A skin lesion imaged with a dermatoscope.
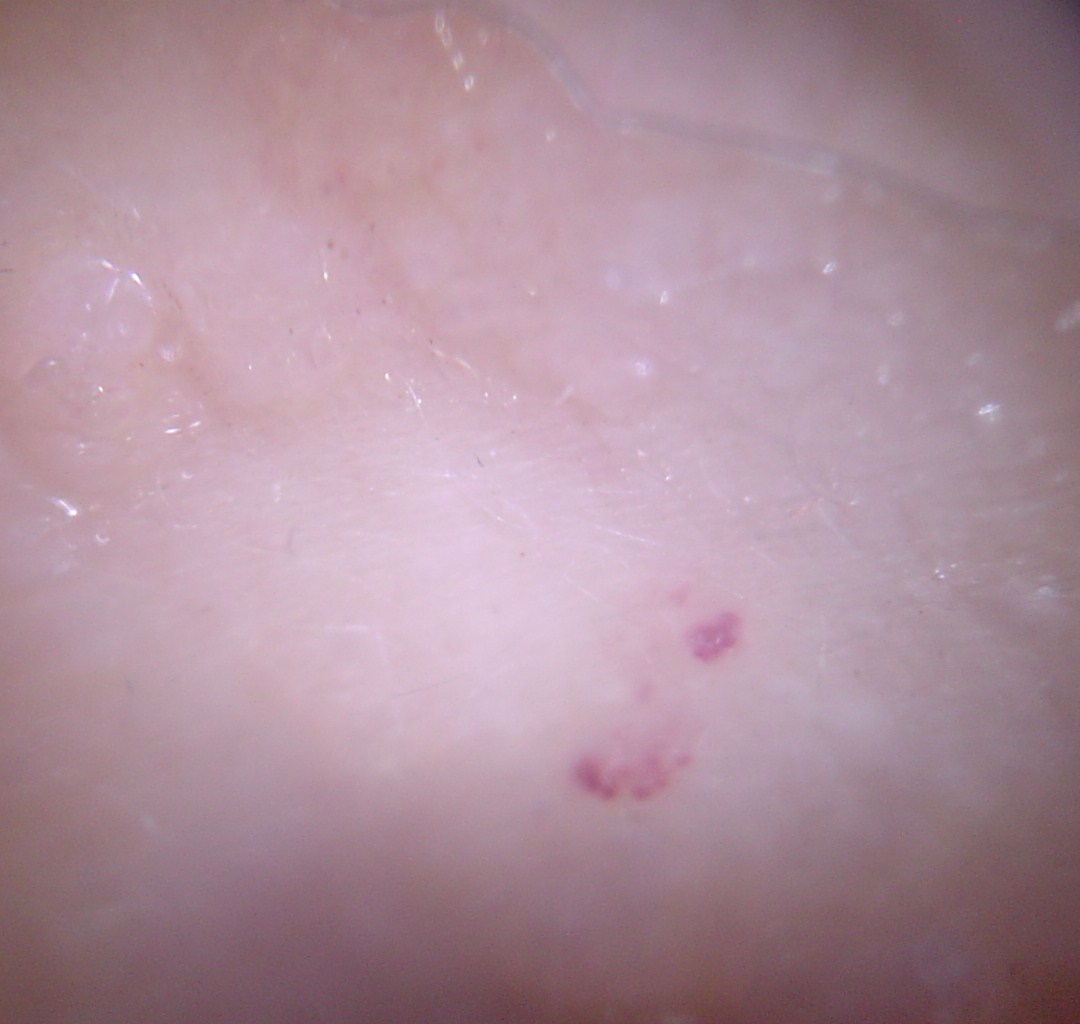Diagnosed as a vascular lesion — a hemangioma.